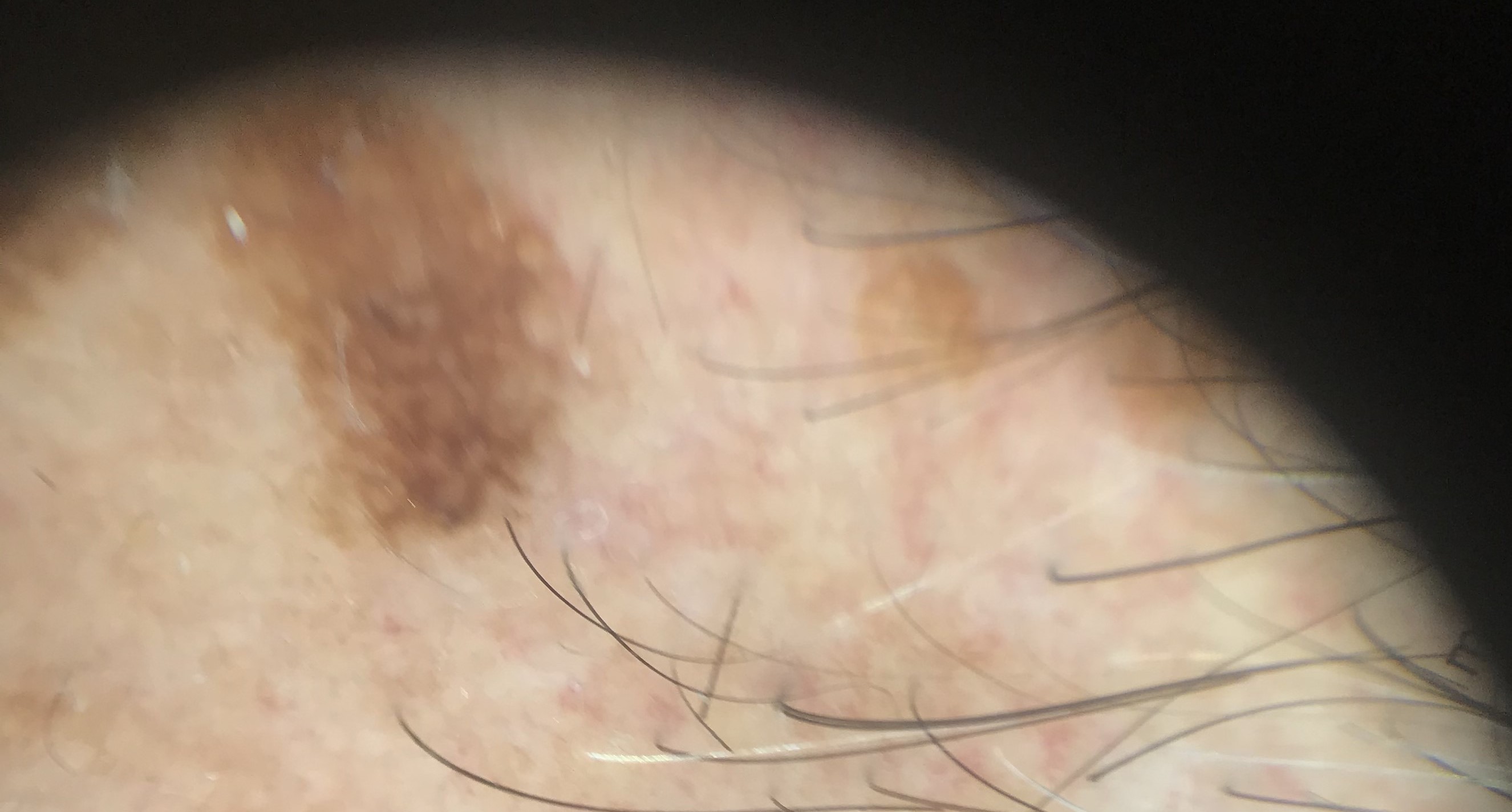A dermoscopy image of a single skin lesion.
The diagnostic label was a benign, keratinocytic lesion — a seborrheic keratosis.